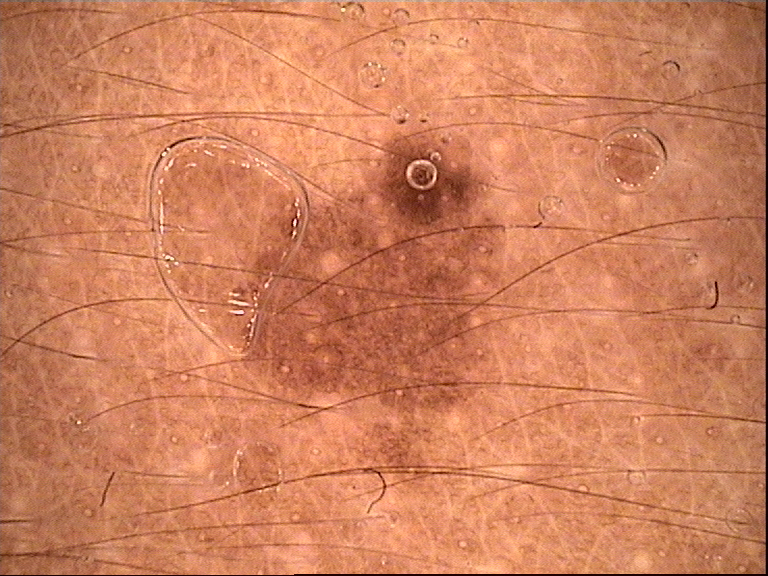class: dysplastic junctional nevus (expert consensus).